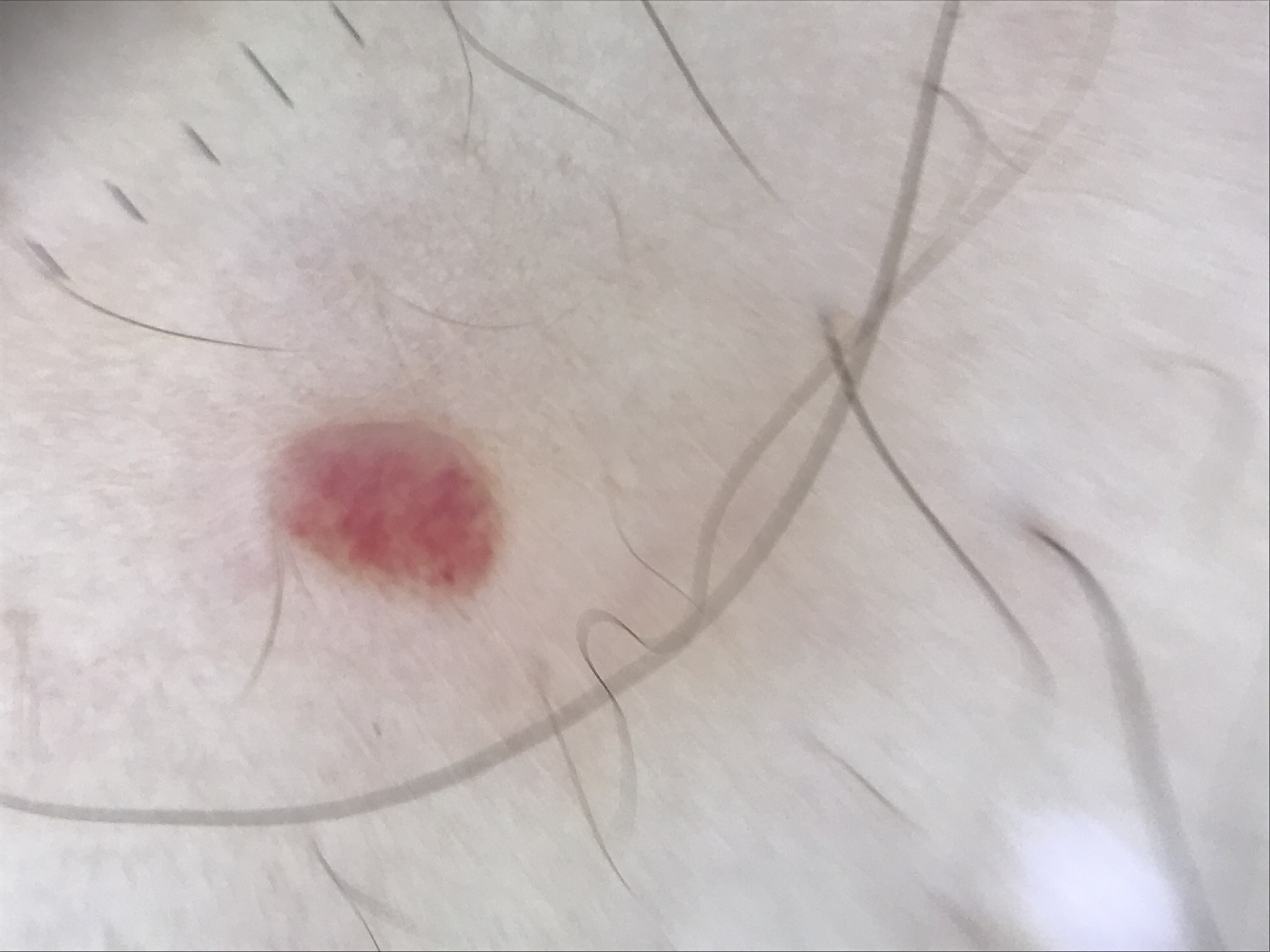Classified as a hemangioma.